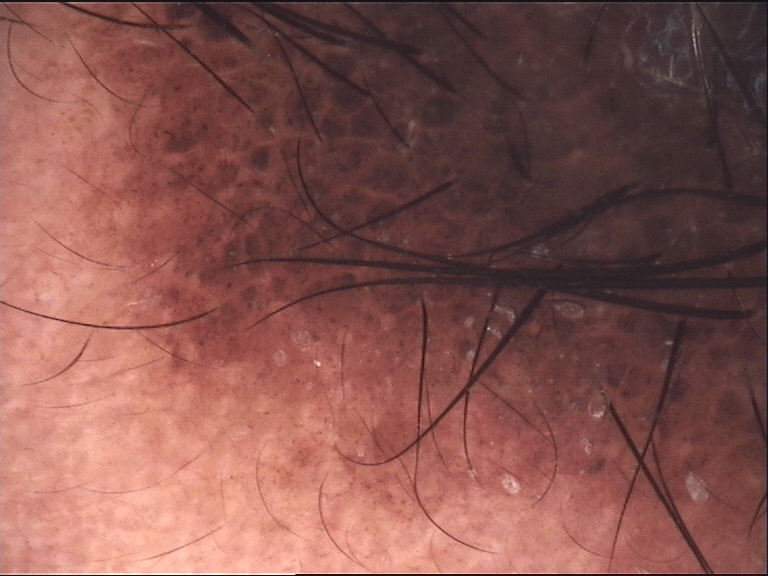A dermoscopy image of a single skin lesion. The diagnosis was a banal lesion — a congenital compound nevus.